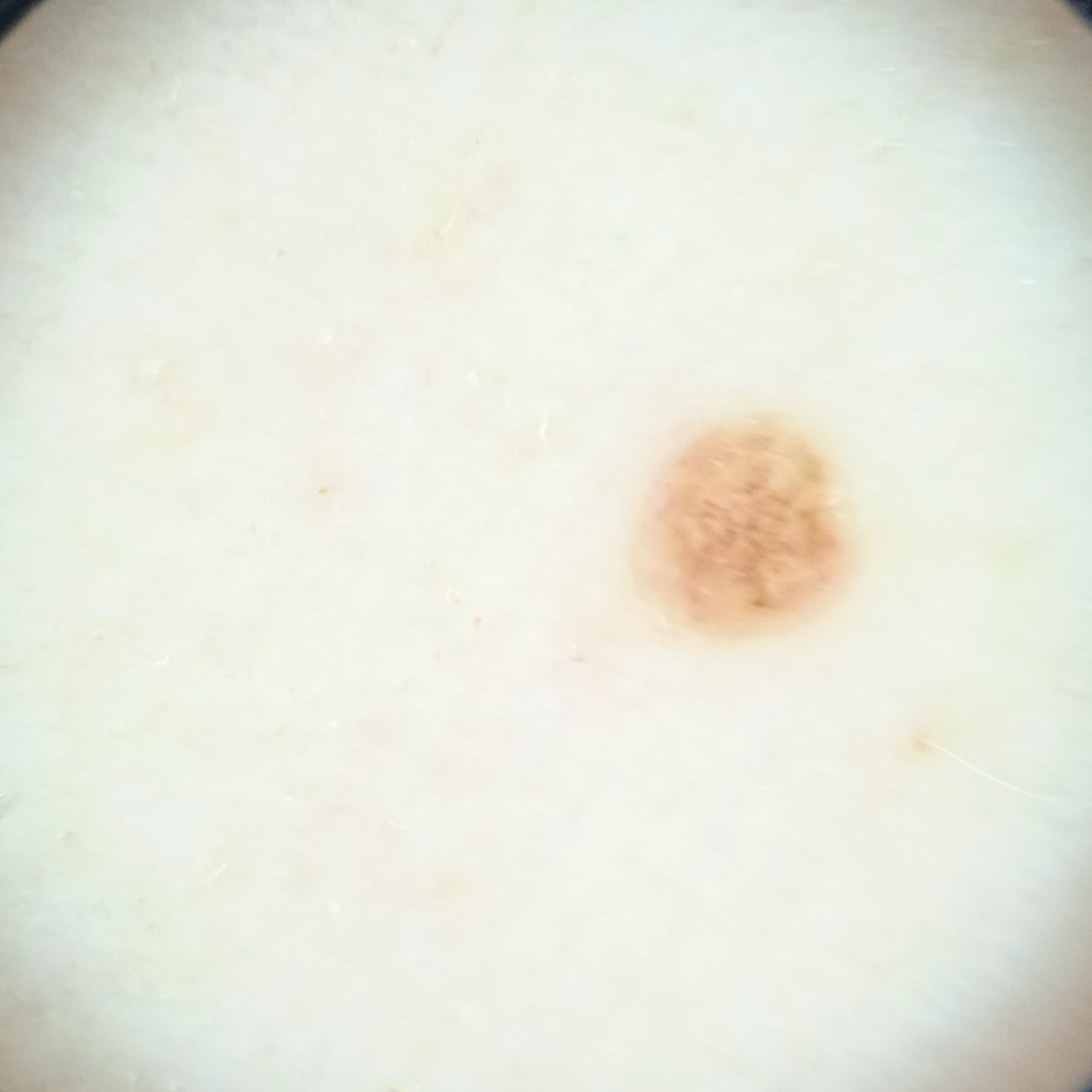| field | value |
|---|---|
| referral context | research study (no referral diagnosis) |
| sun reaction | skin reddens painfully with sun exposure |
| relevant history | no personal history of cancer, no immunosuppression |
| subject | female, age 50 |
| diagnosis | melanocytic nevus (dermatologist consensus) |